A clinical close-up photograph of a skin lesion; a patient aged 39: 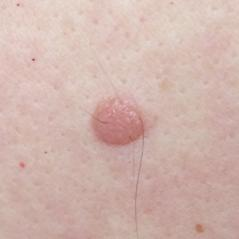region: the chest
reported symptoms: growth, elevation
diagnostic label: nevus (clinical consensus)